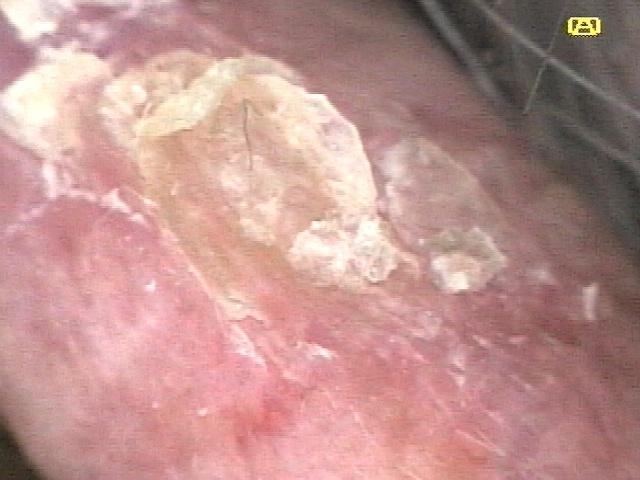| feature | finding |
|---|---|
| subject | male, in their mid-80s or older |
| image type | contact-polarized dermoscopy |
| assessment | Solar or actinic keratosis |